This image was taken at a distance.
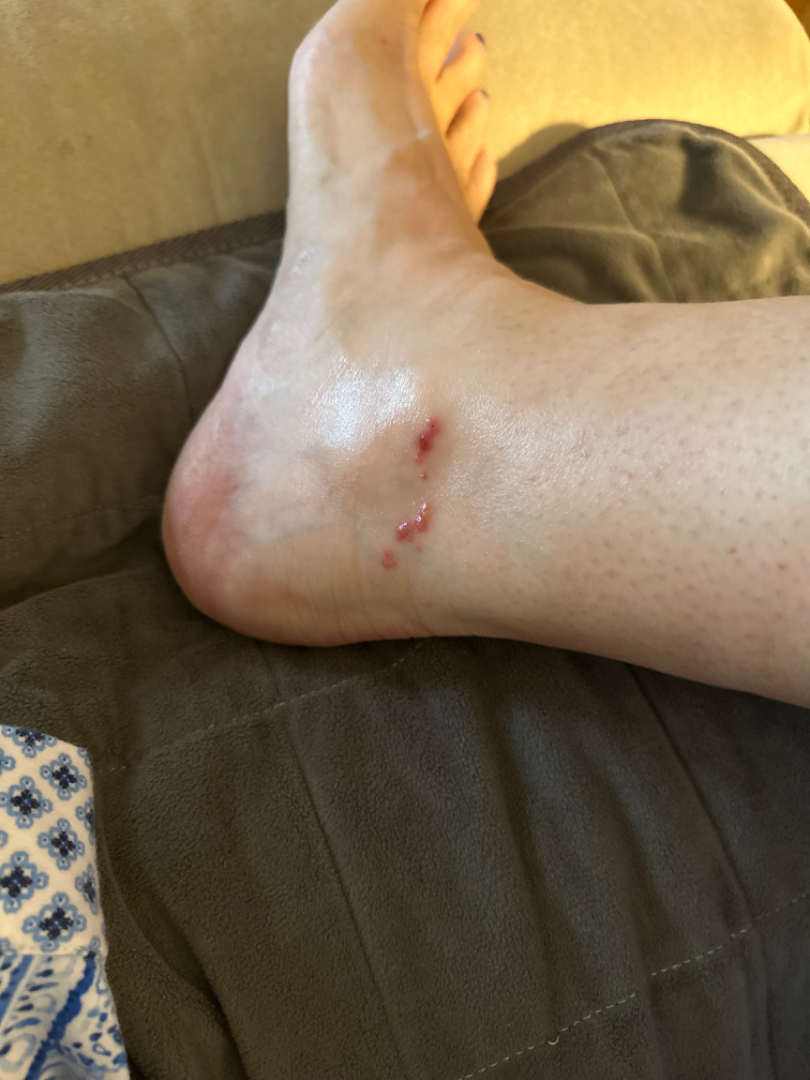assessment=could not be assessed.